A clinical photograph of a skin lesion: 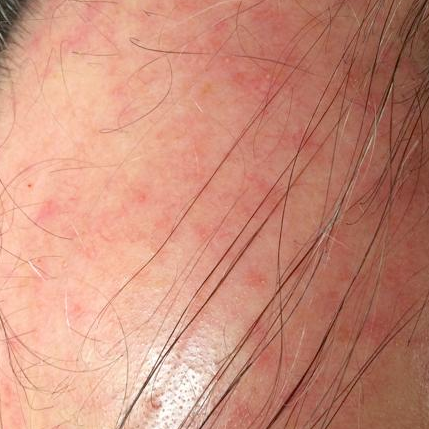Conclusion: The clinical impression was an actinic keratosis.